This is a close-up image: 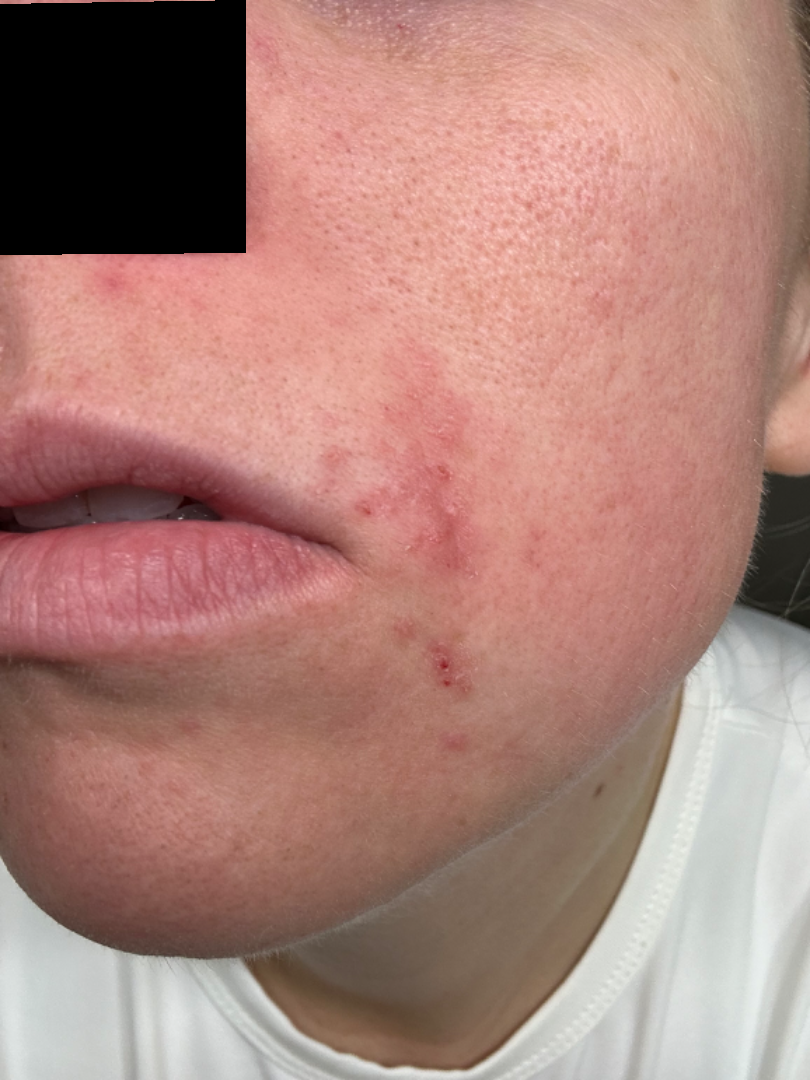The reviewing dermatologist's impression was: Perioral Dermatitis (most likely); Impetigo (considered); Herpes Simplex (considered).